The photo was captured at an angle. Male contributor, age 18–29. The head or neck, back of the torso and arm are involved.
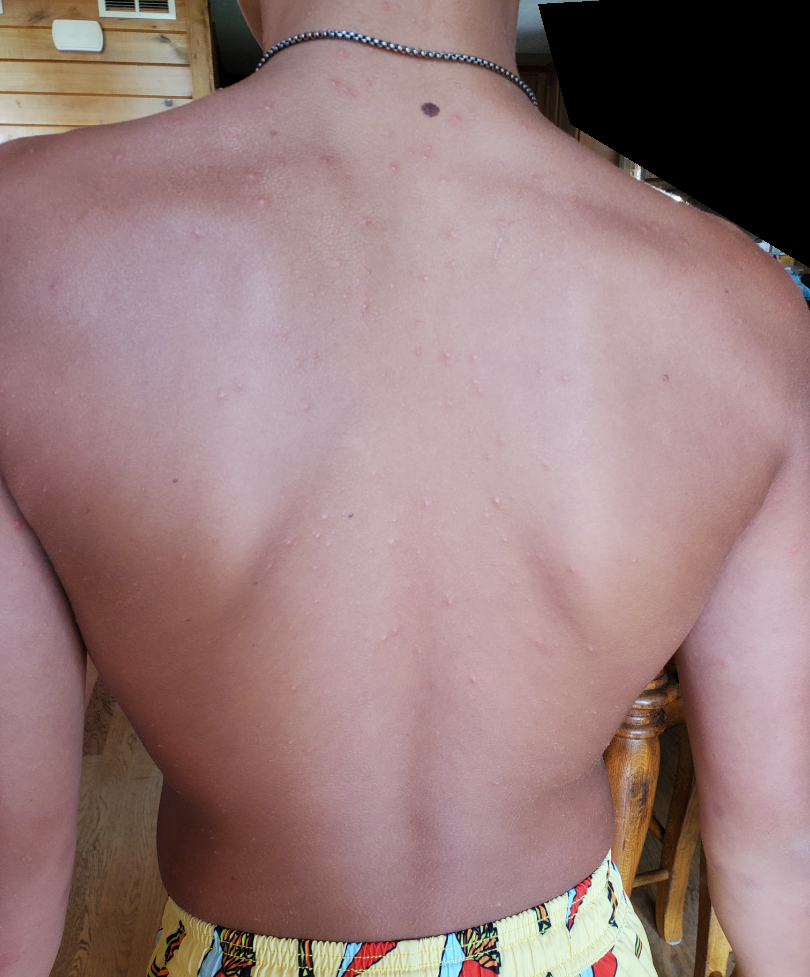Consistent with Folliculitis.